A dermoscopic image of a skin lesion.
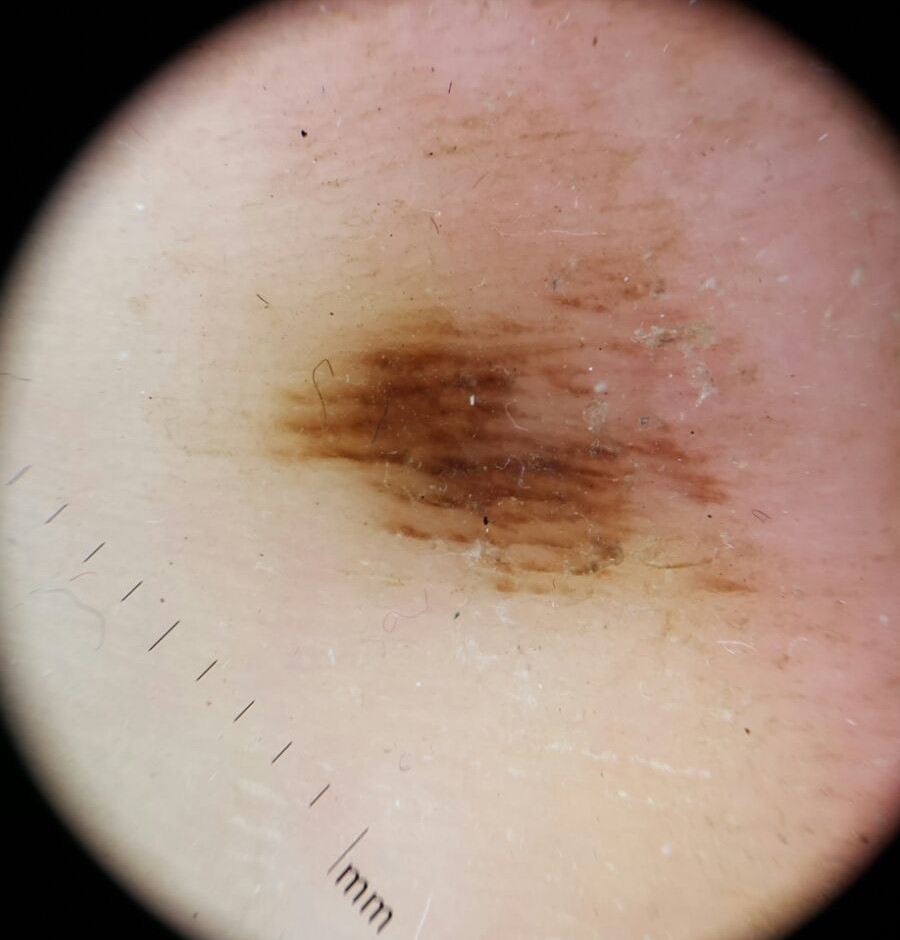diagnosis: acral dysplastic junctional nevus (expert consensus).